A dermoscopic image of a skin lesion.
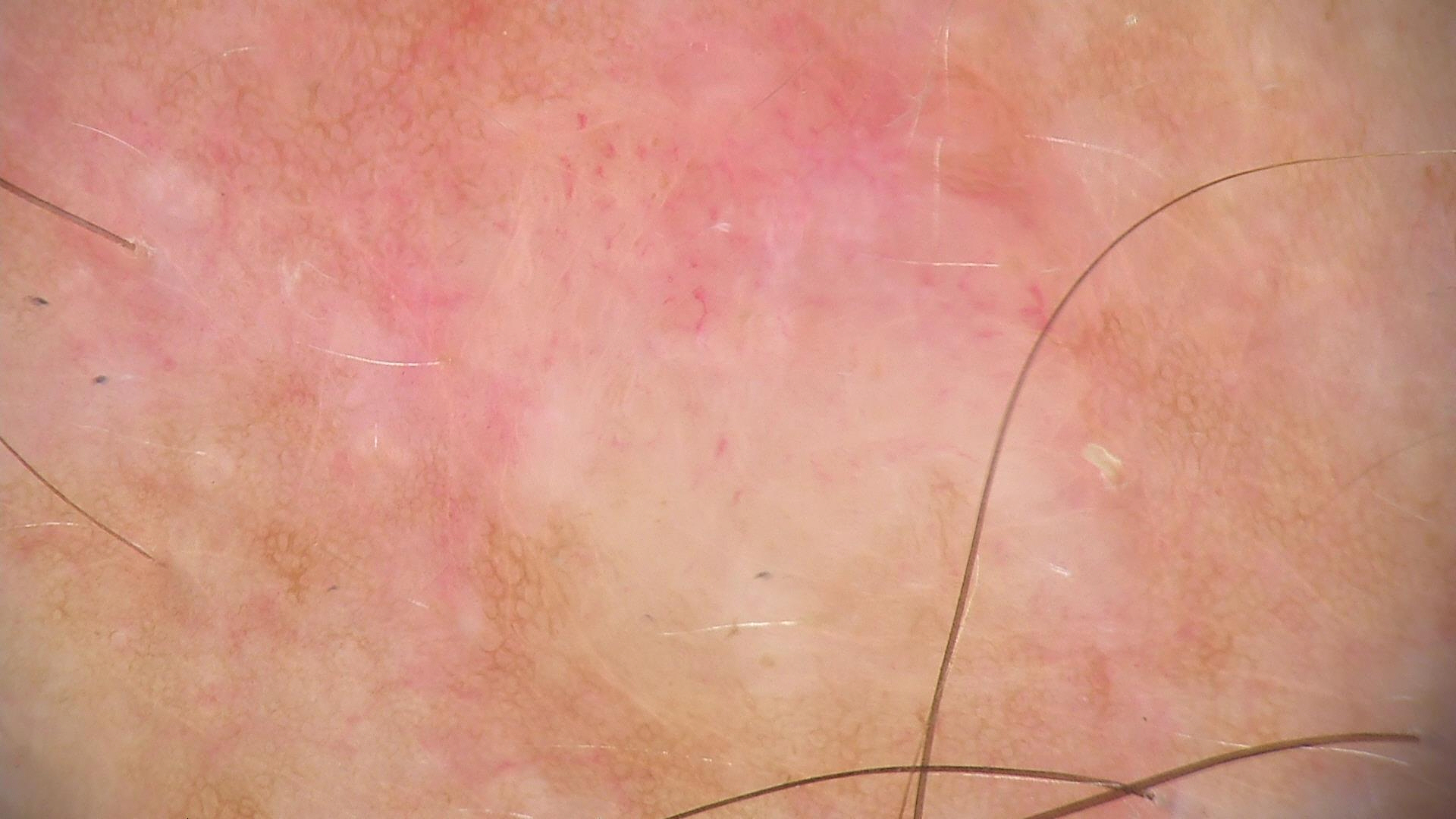assessment: dermal nevus (expert consensus).